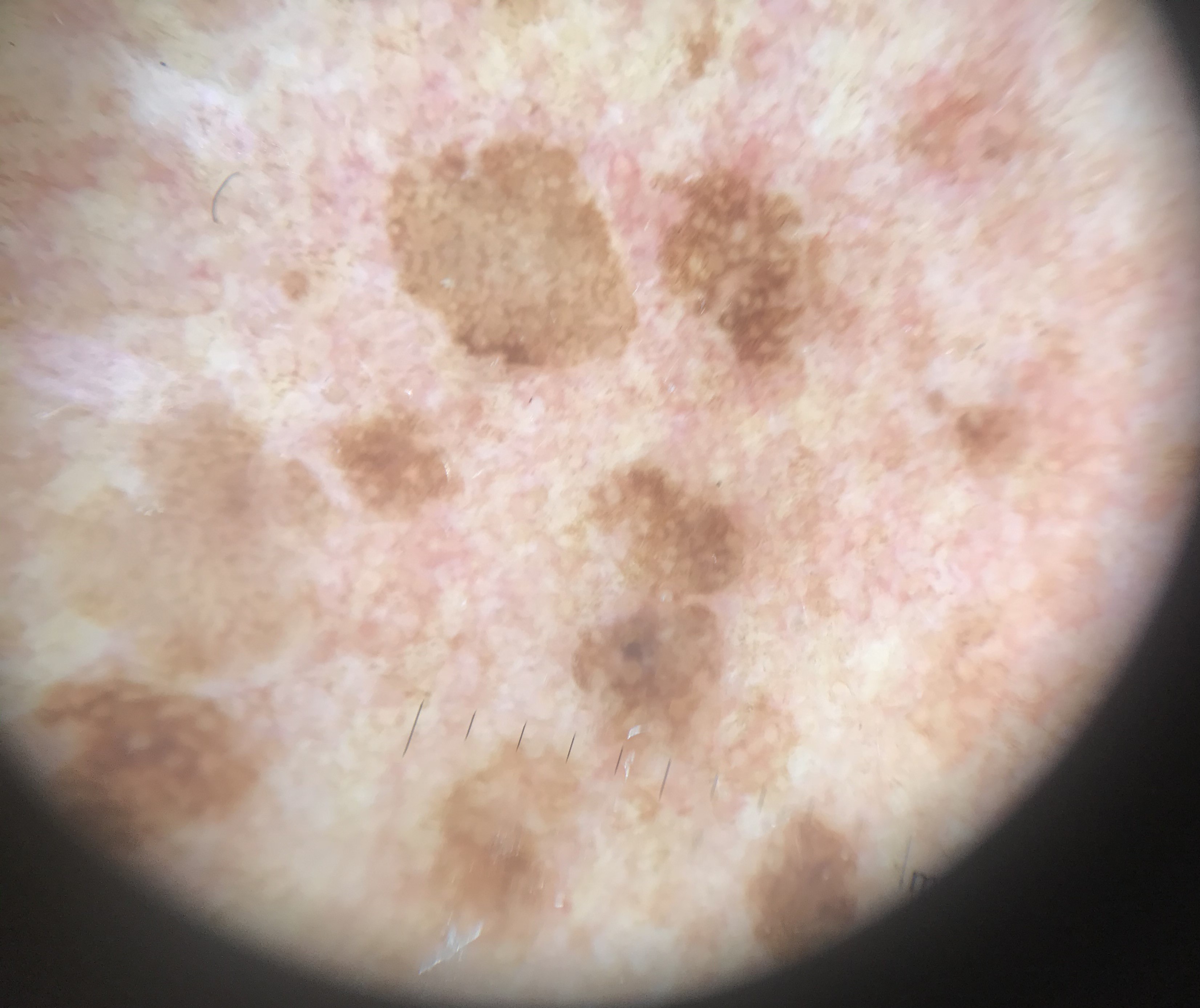Findings:
A dermoscopic photograph of a skin lesion.
Impression:
The diagnosis was a benign, keratinocytic lesion — a seborrheic keratosis.